The arm is involved · no constitutional symptoms were reported · the condition has been present for about one day · the patient notes the lesion is flat · skin tone: Fitzpatrick III; non-clinician graders estimated 2 on the Monk Skin Tone · the patient is a female aged 18–29 · the photograph is a close-up of the affected area.
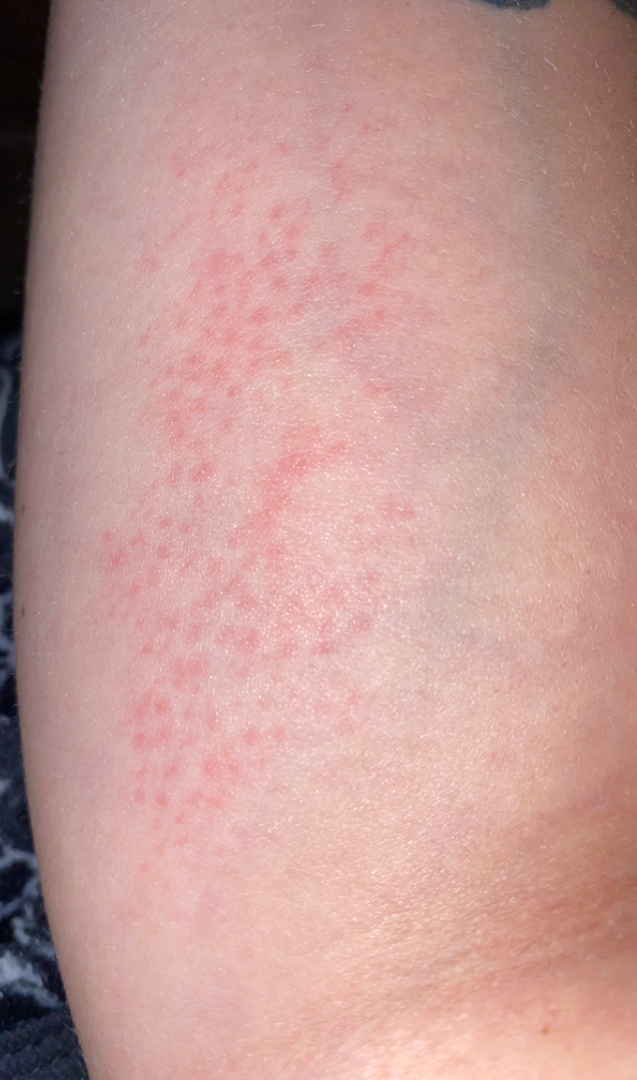* diagnostic considerations: most consistent with Irritant Contact Dermatitis